The affected area is the arm. Skin tone: FST III. This is a close-up image. The patient notes bothersome appearance and itching. The condition has been present for less than one week. Texture is reported as raised or bumpy and rough or flaky:
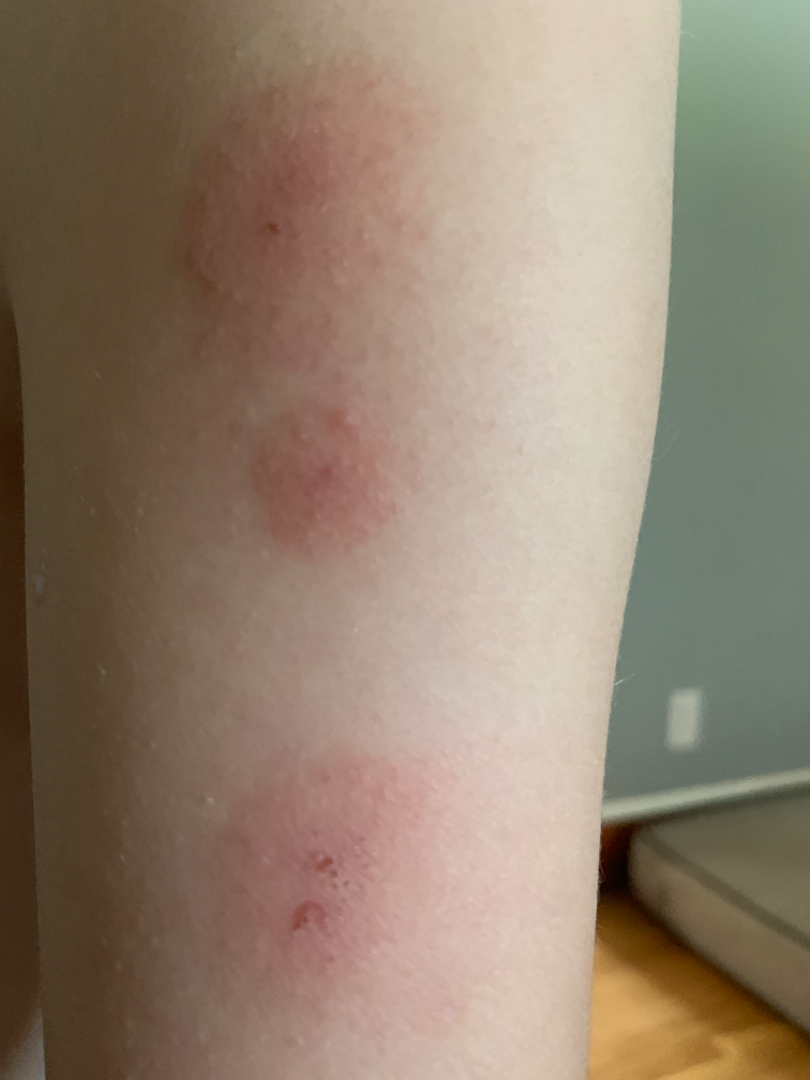{
  "differential": {
    "leading": [
      "Eczema"
    ]
  }
}